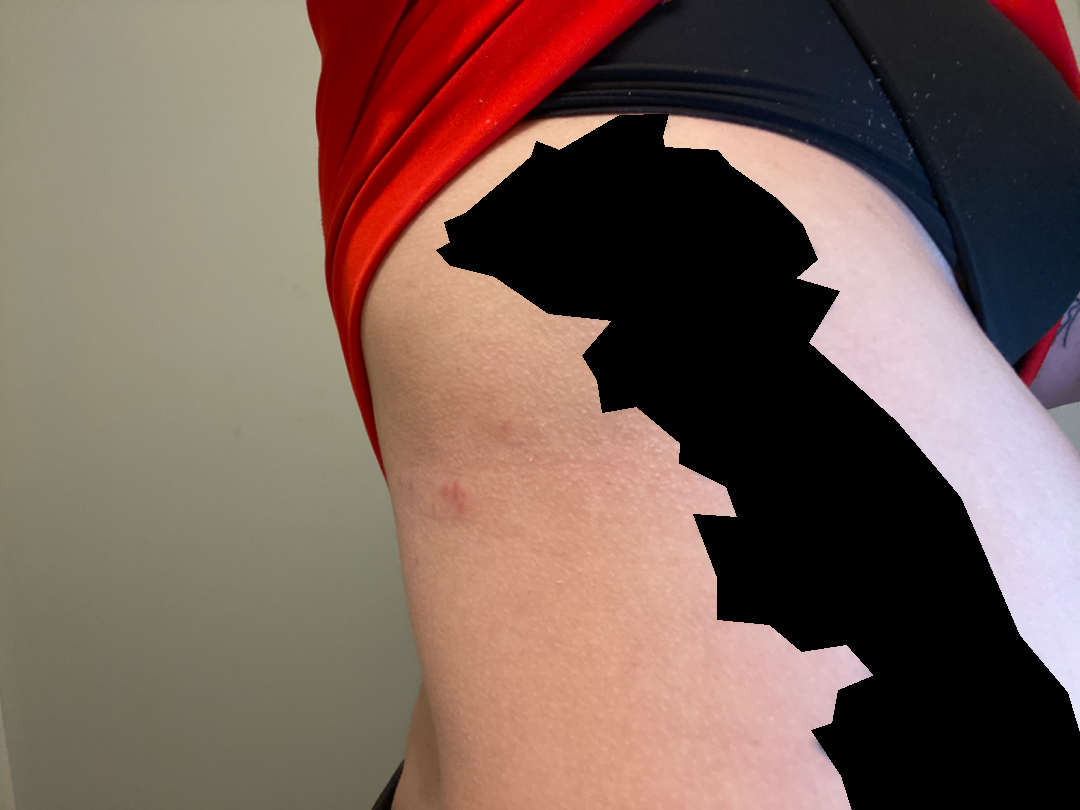Q: What was the assessment?
A: indeterminate